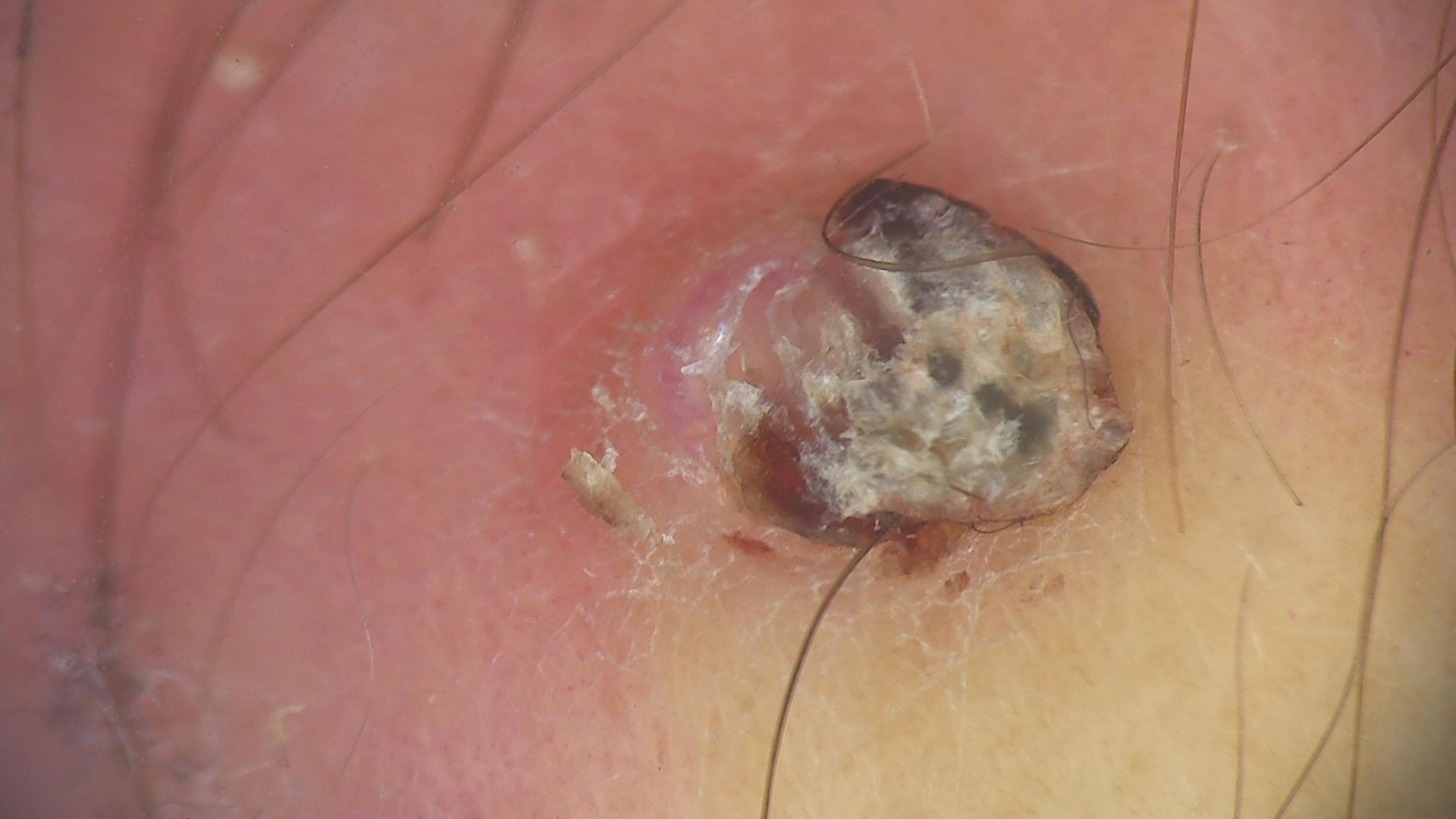subtype: keratinocytic | label: squamous cell carcinoma (biopsy-proven).